A skin lesion imaged with a dermatoscope; the patient reports a personal history of cancer and a personal history of skin cancer; the patient describes having a moderate number of moles; a male patient 77 years of age; the patient says their skin reddens with sun exposure; acquired for a research image collection, with no referral diagnosis — 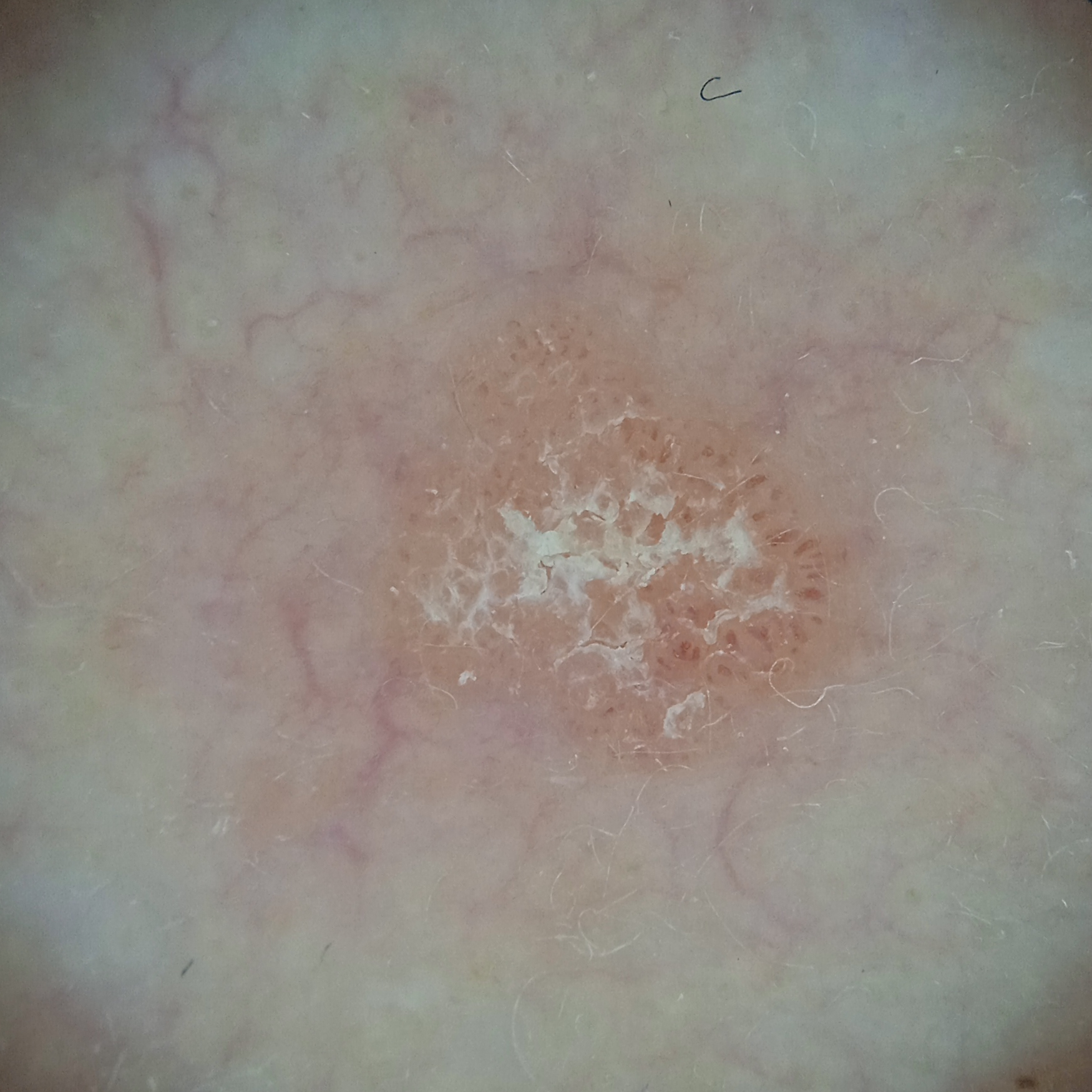site: the face | lesion size: 4.3 mm | diagnosis: actinic keratosis (dermatologist consensus).